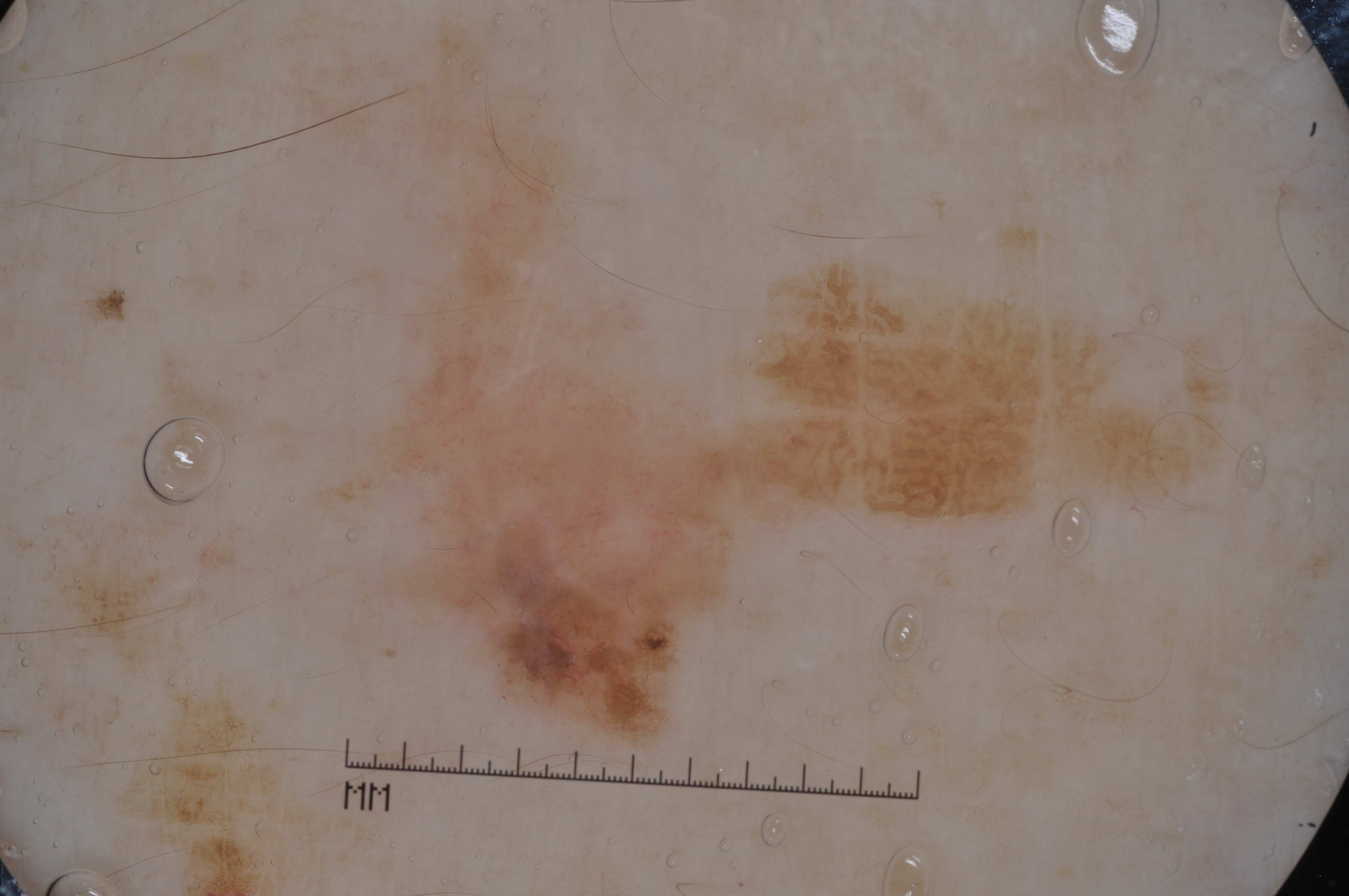Q: Who is the patient?
A: male, aged 83 or over
Q: How was this image acquired?
A: dermoscopy
Q: What does dermoscopy show?
A: milia-like cysts, pigment network, and negative network; absent: streaks
Q: Where is the lesion in the image?
A: left=383, top=70, right=744, bottom=749
Q: Lesion extent?
A: moderate
Q: What did the assessment conclude?
A: a melanoma